The patient reports bothersome appearance, itching and darkening · an image taken at an angle · texture is reported as flat · the patient is 30–39, male · the patient described the issue as a rash · present for less than one week · the affected area is the leg:
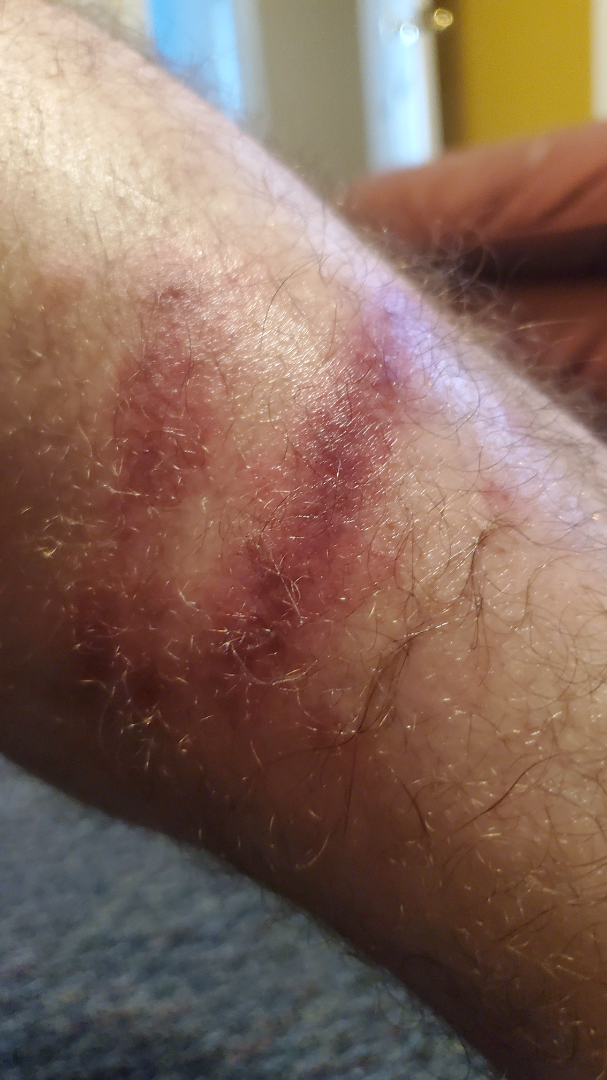• diagnostic considerations — Abrasion, scrape, or scab (27%); Flagellate erythema (27%); Allergic Contact Dermatitis (14%); Skin infection (11%); Dermatomyositis (11%); Animal bite - wound (9%)